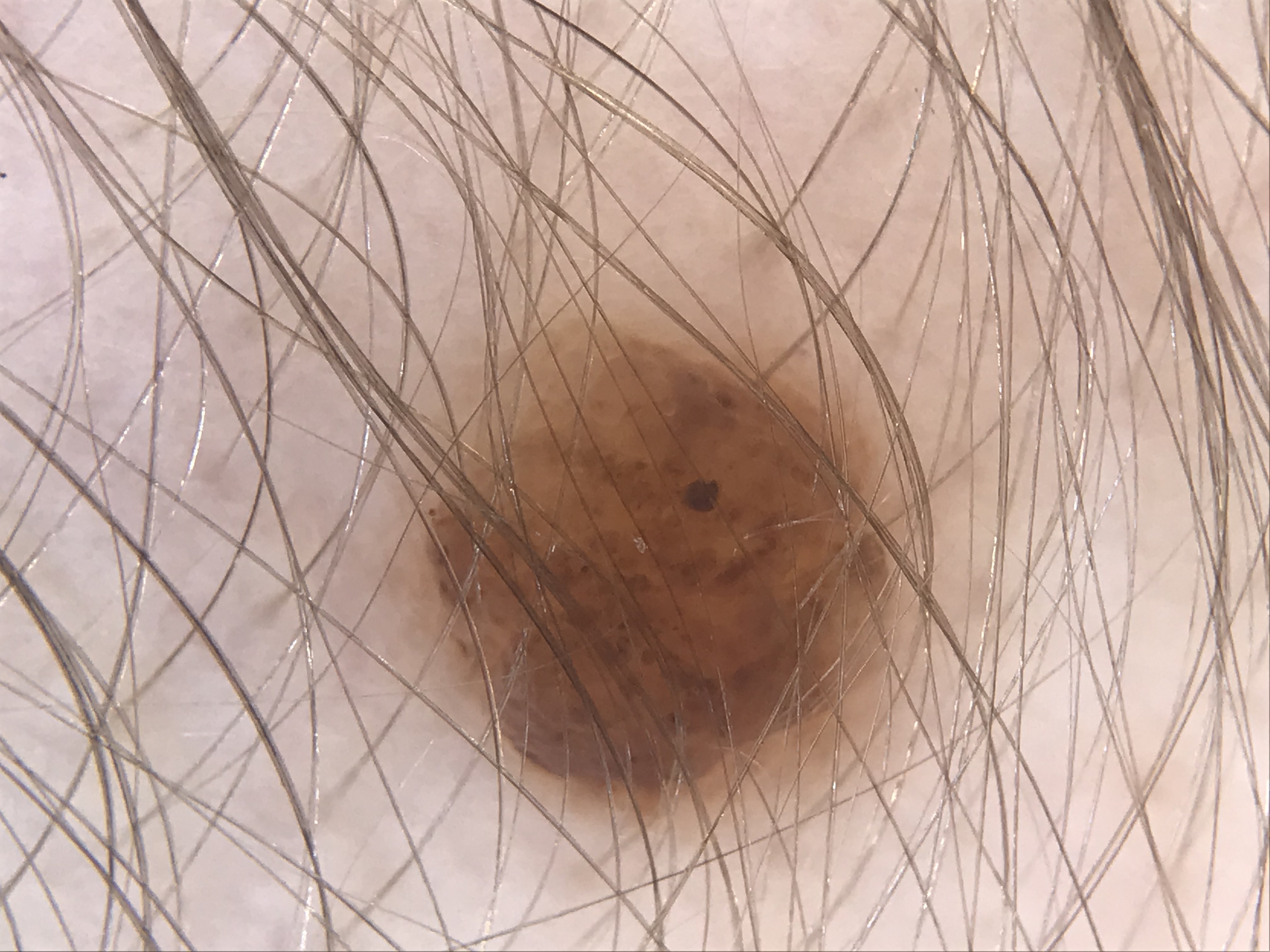This is a banal lesion. The diagnostic label was a compound nevus.